This is a close-up image:
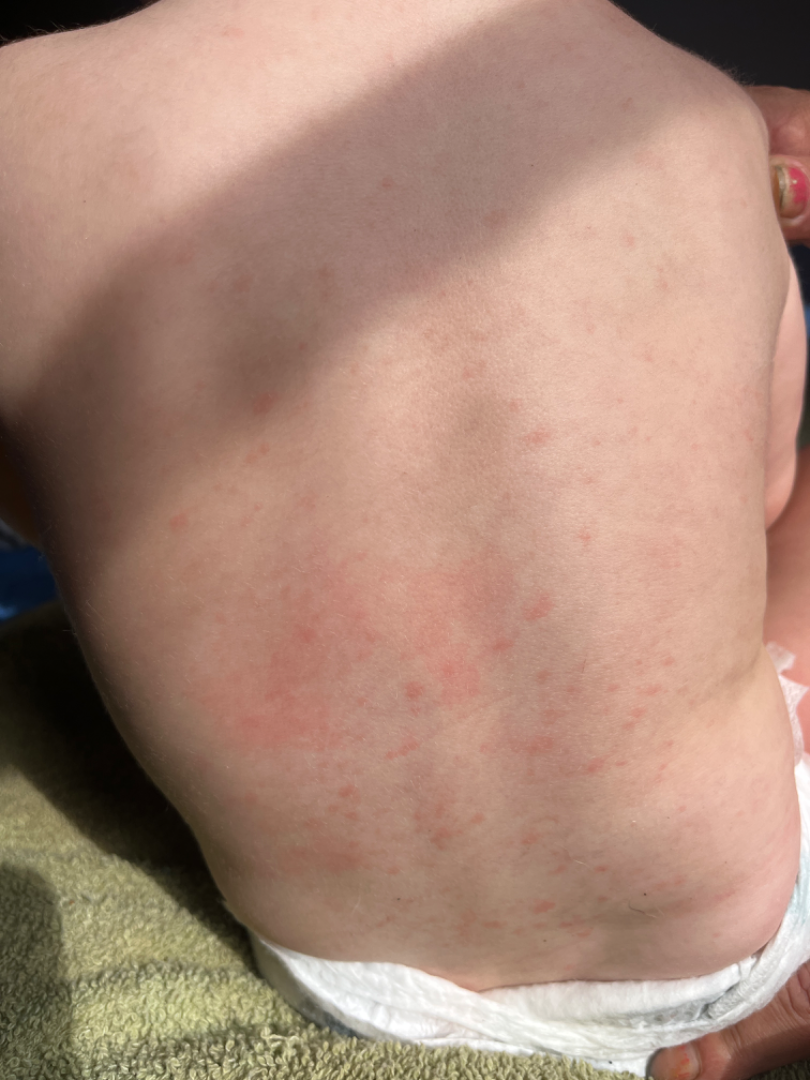The skin condition could not be confidently assessed from this image.